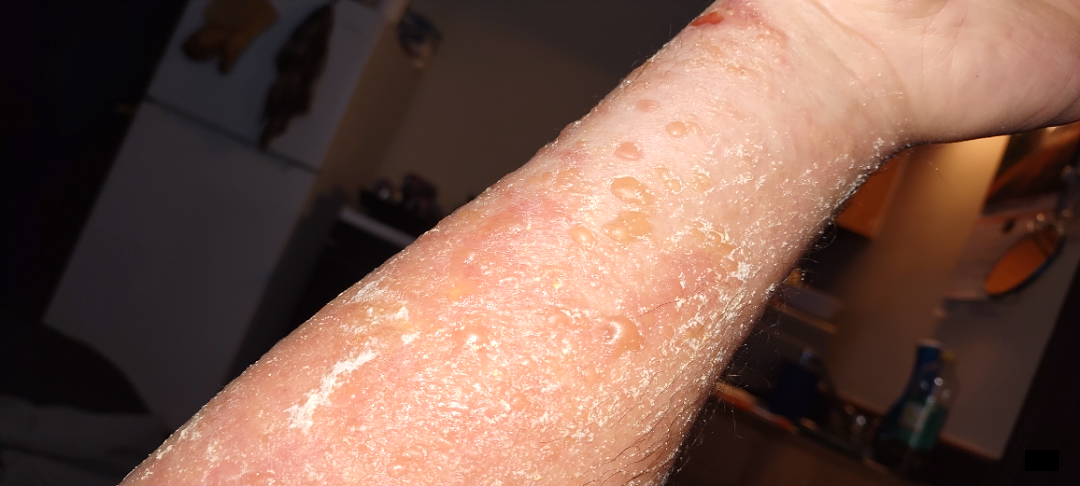Q: How was the photo taken?
A: close-up
Q: Who is the patient?
A: male
Q: Anatomic location?
A: arm and front of the torso
Q: What conditions are considered?
A: Bullous Pemphigoid (weight 0.54); Burn of skin (weight 0.23); Allergic Contact Dermatitis (weight 0.23)